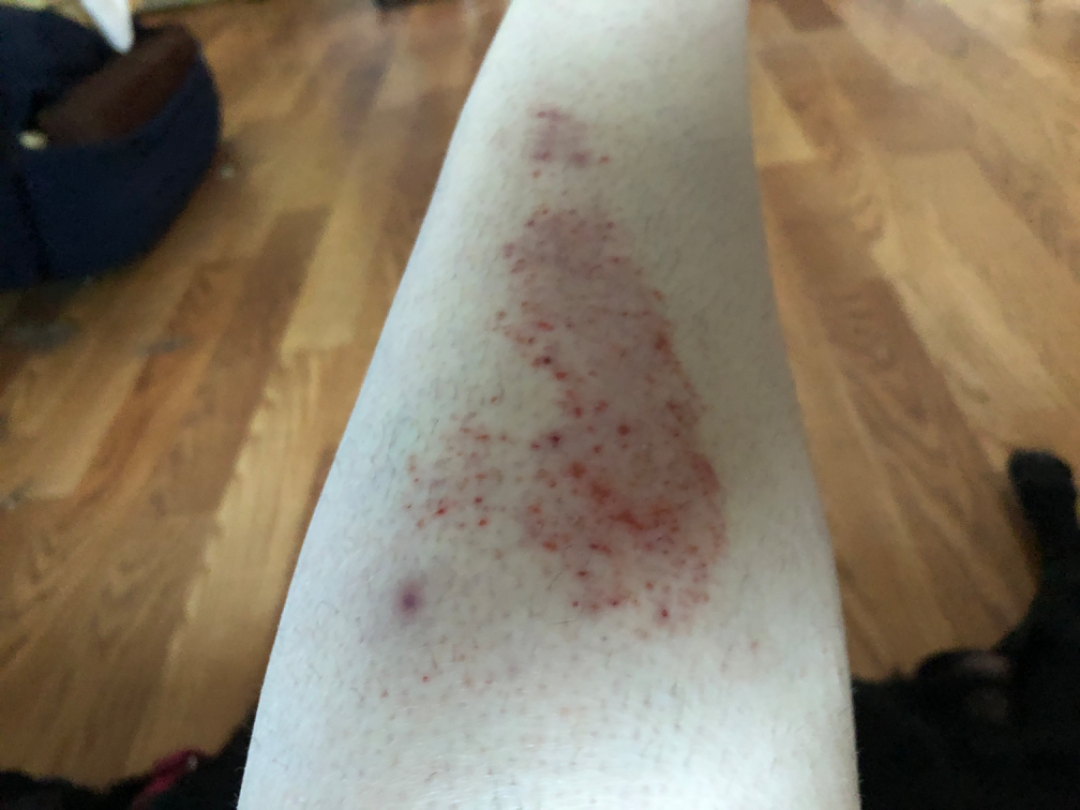This is a close-up image. Texture is reported as rough or flaky, fluid-filled and raised or bumpy. The patient is a female aged 40–49. The contributor notes burning, itching, pain, enlargement, bothersome appearance and bleeding. The contributor notes the condition has been present for three to twelve months. Skin tone: Fitzpatrick skin type II; lay graders estimated MST 1. Located on the leg. Abrasion, scrape, or scab (weight 0.54); Tinea (weight 0.23); Eczema (weight 0.23).